A clinical photo of a skin lesion taken with a smartphone — 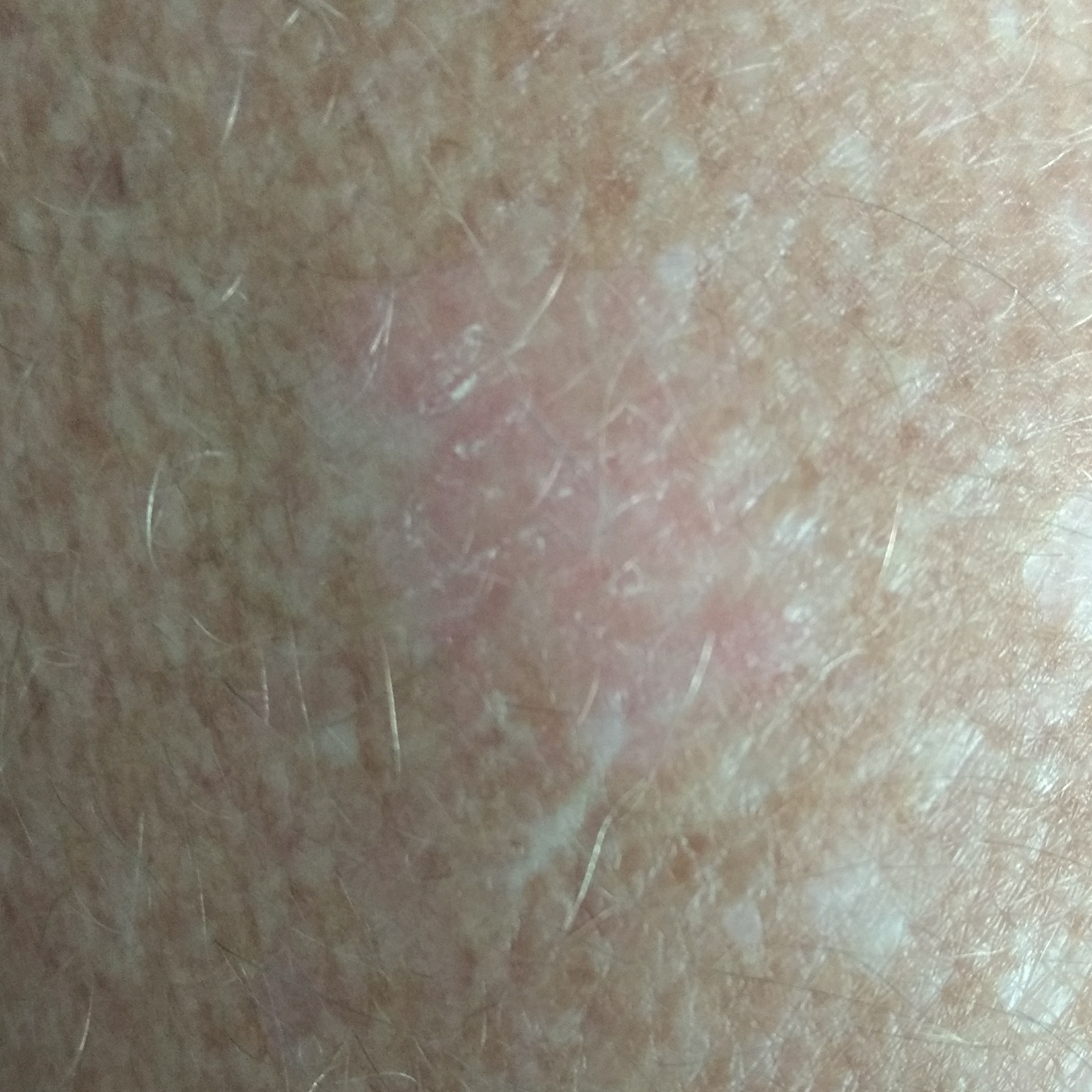The lesion is located on a forearm. Per patient report, the lesion itches. The clinical impression was an actinic keratosis.